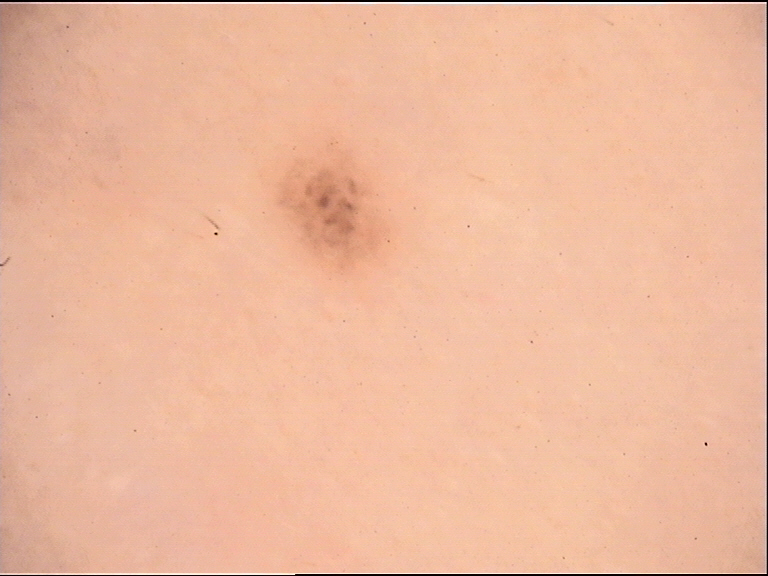diagnostic label: dysplastic junctional nevus (expert consensus).